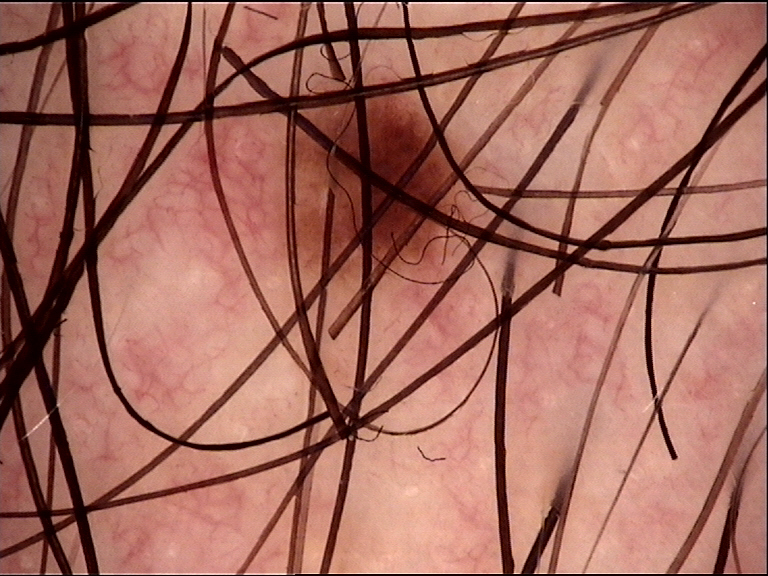class — junctional nevus (expert consensus)